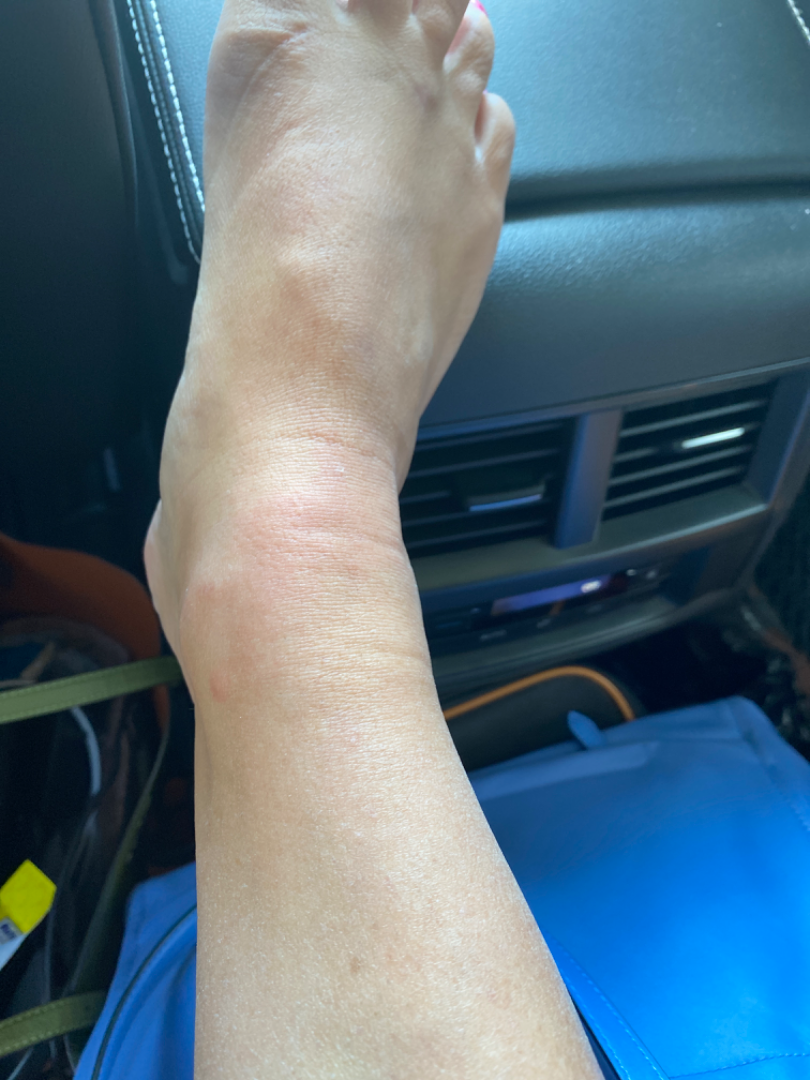Q: Could the case be diagnosed?
A: no skin condition identified